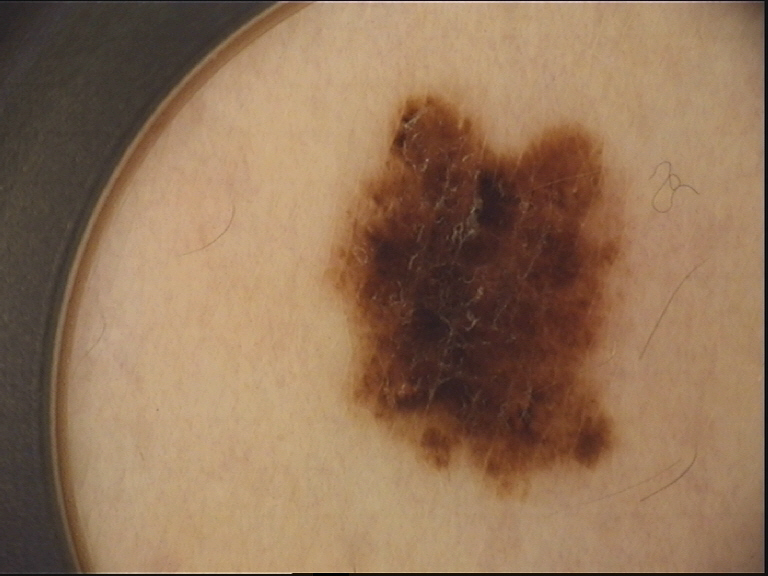Labeled as a dysplastic compound nevus.